This is a dermoscopic photograph of a skin lesion. A male patient roughly 35 years of age.
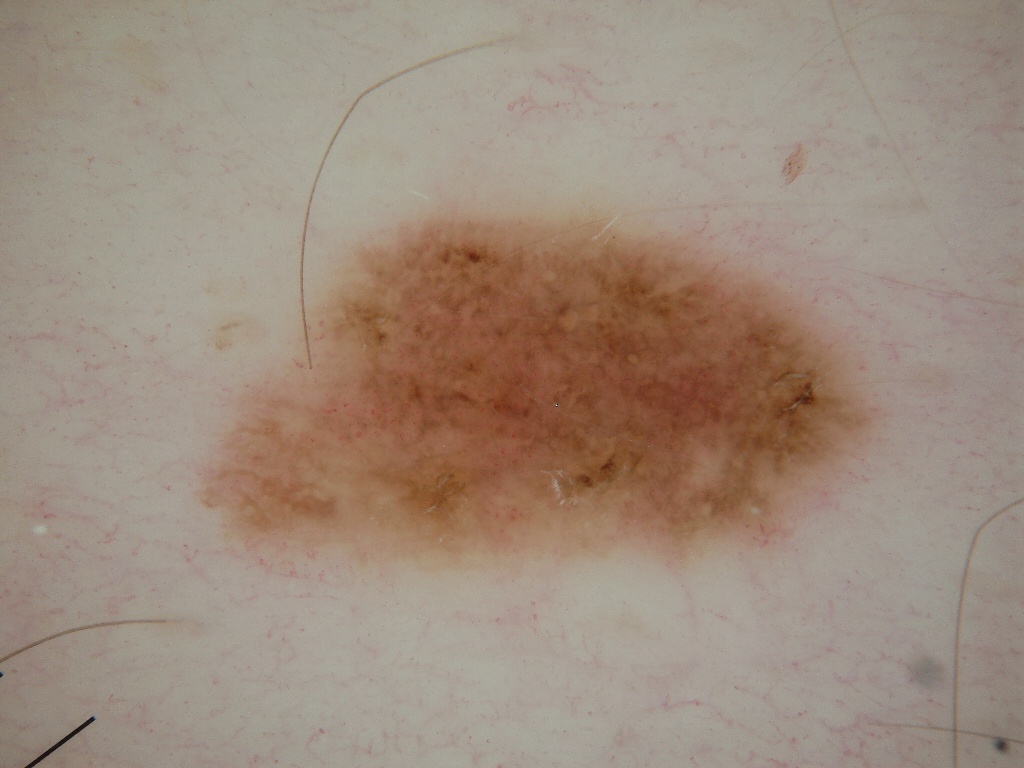The lesion occupies roughly 24% of the field. On dermoscopy, the lesion shows globules, milia-like cysts, and pigment network, with no negative network or streaks. In (x1, y1, x2, y2) order, the lesion is bounded by bbox=[196, 201, 891, 571]. The clinical diagnosis was a melanocytic nevus, a benign skin lesion.